This is a close-up image: 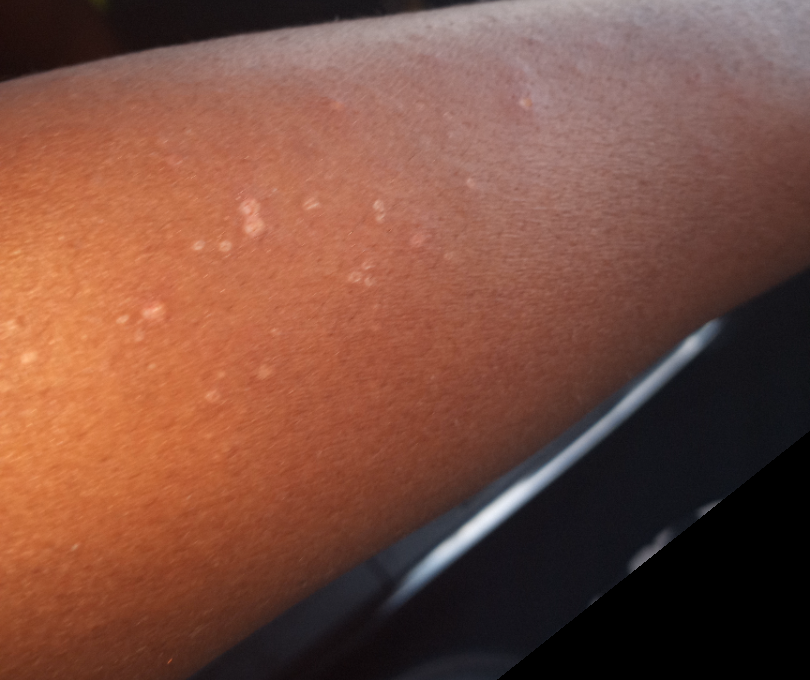A single dermatologist reviewed the case: consistent with Idiopathic guttate hypomelanosis.